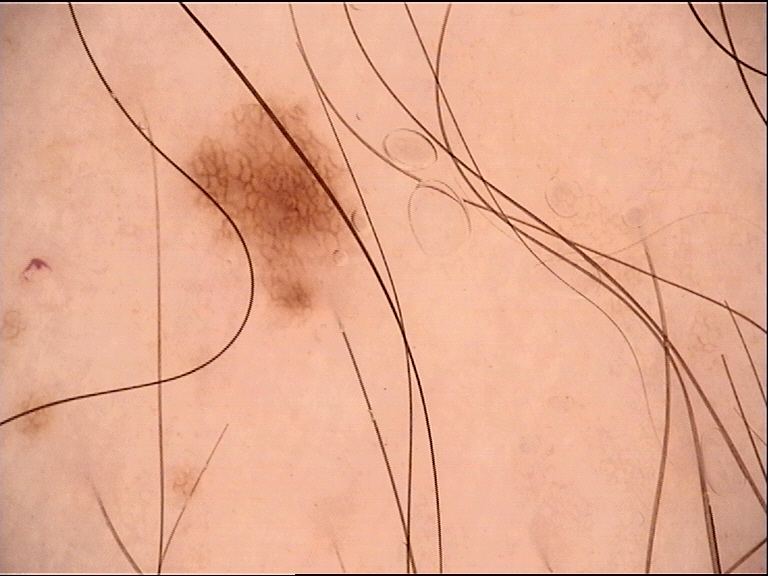A dermoscopic image of a skin lesion.
The diagnostic label was a dysplastic junctional nevus.